The photograph is a close-up of the affected area. The patient is a female aged 40–49. Located on the top or side of the foot: 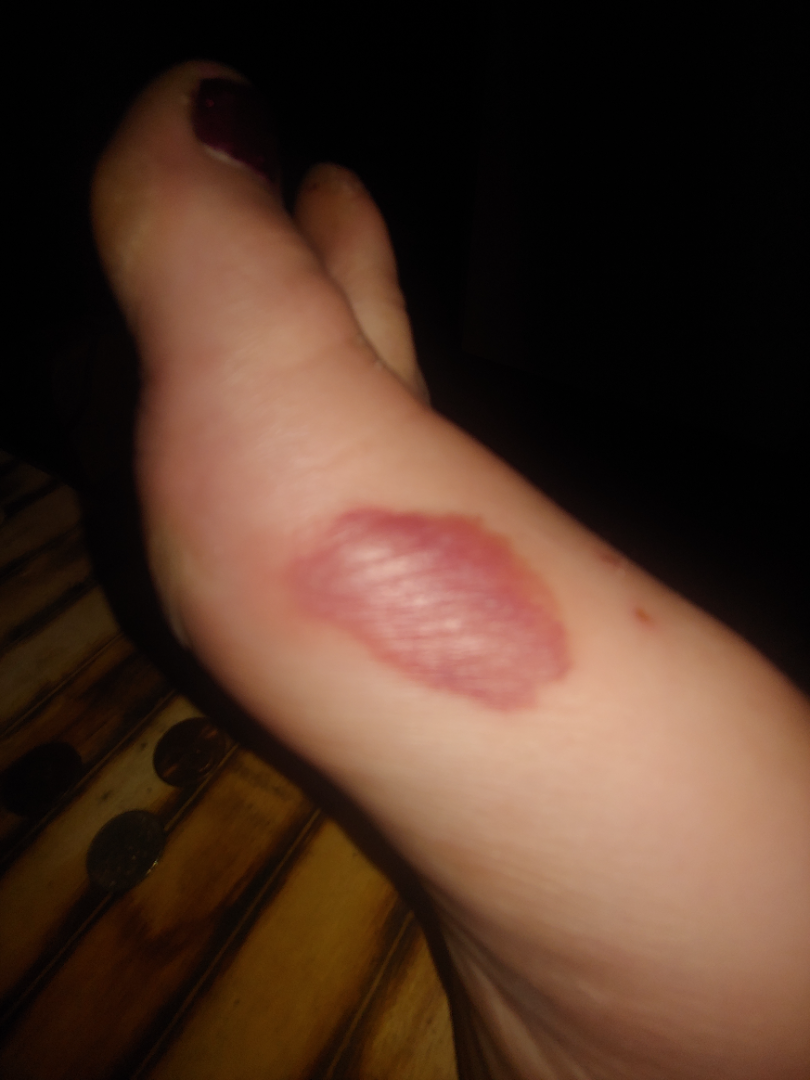Notes:
* assessment: not assessable